The photograph was taken at an angle — 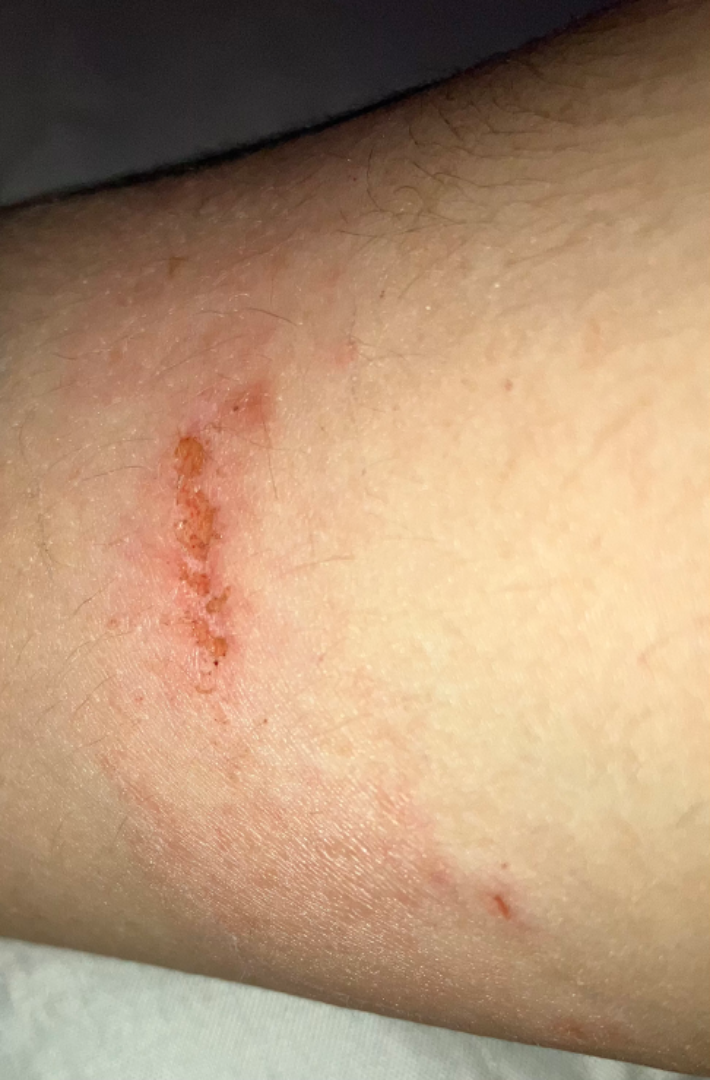Impression:
The reviewer was unable to grade this case for skin condition.